A dermoscopy image of a single skin lesion: 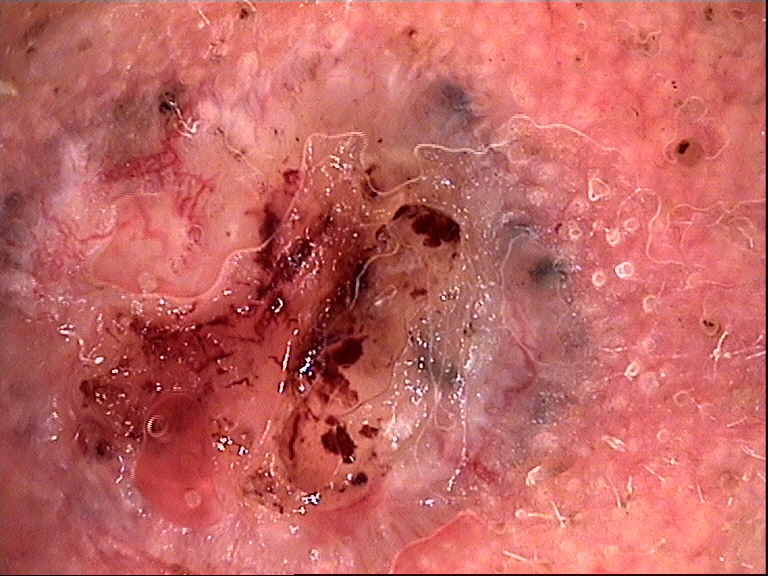{
  "diagnosis": {
    "name": "basal cell carcinoma",
    "code": "bcc",
    "malignancy": "malignant",
    "super_class": "non-melanocytic",
    "confirmation": "histopathology"
  }
}